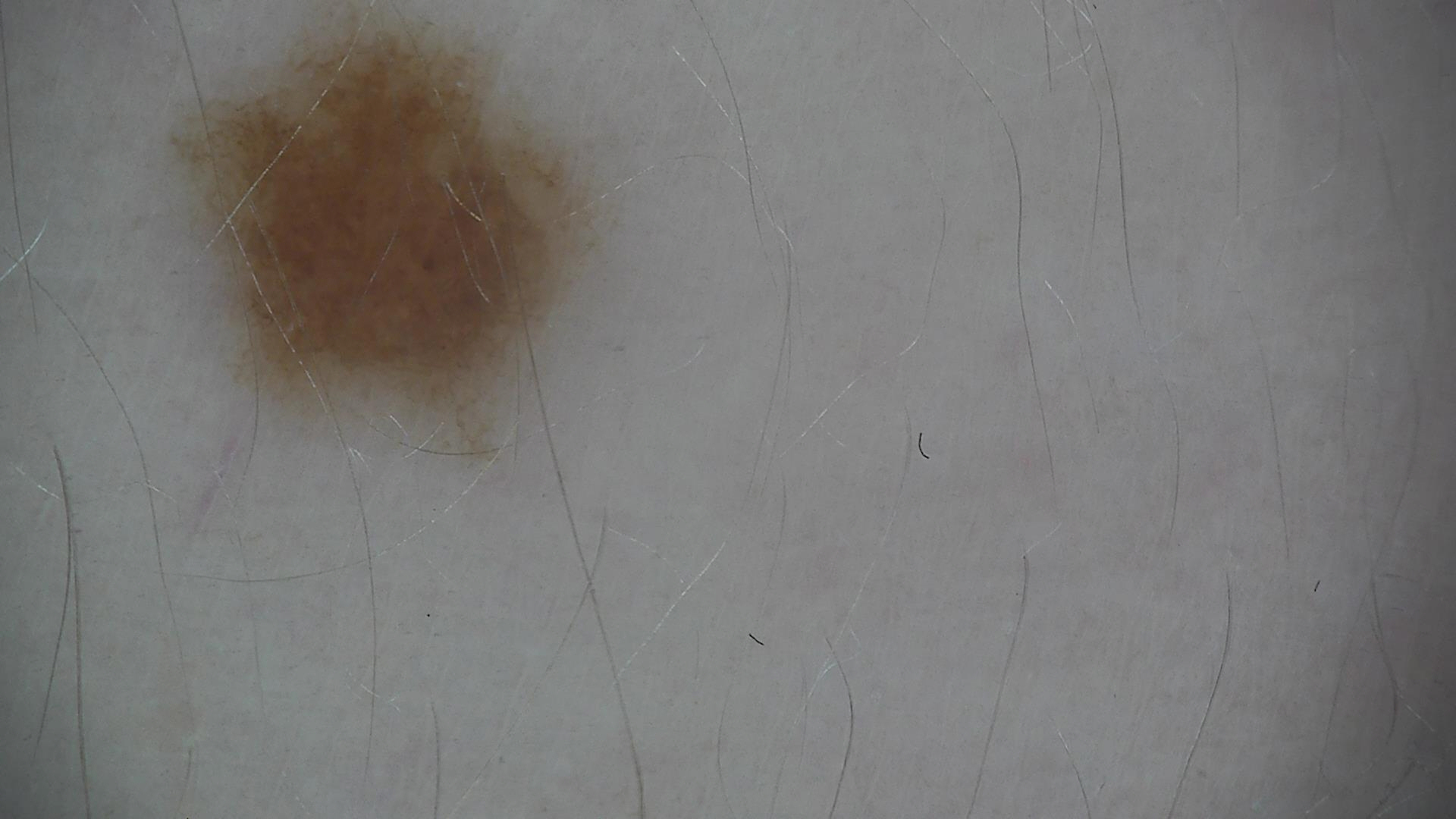Findings:
A dermoscopic image of a skin lesion.
Conclusion:
The diagnosis was a benign lesion — a dysplastic junctional nevus.